This image was taken at a distance, the patient considered this a rash, the lesion is associated with itching, Fitzpatrick skin type IV; human graders estimated MST 4, the condition has been present for less than one week, the affected area is the arm and leg: 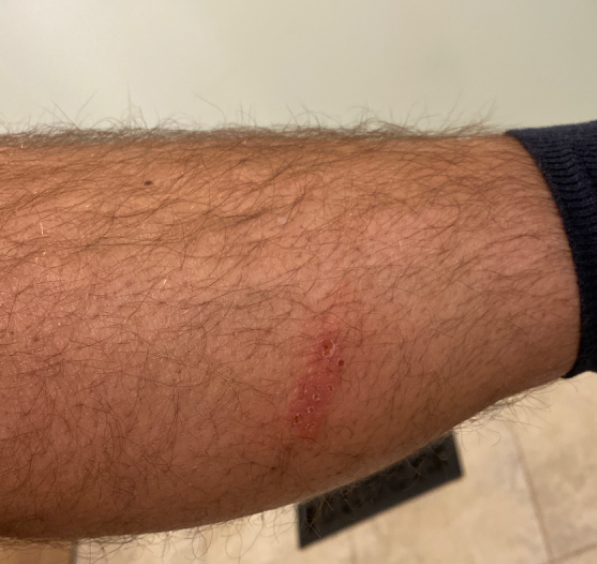Assessment: The case was difficult to assess from the available photograph.